The photograph is a close-up of the affected area. Fitzpatrick phototype III: 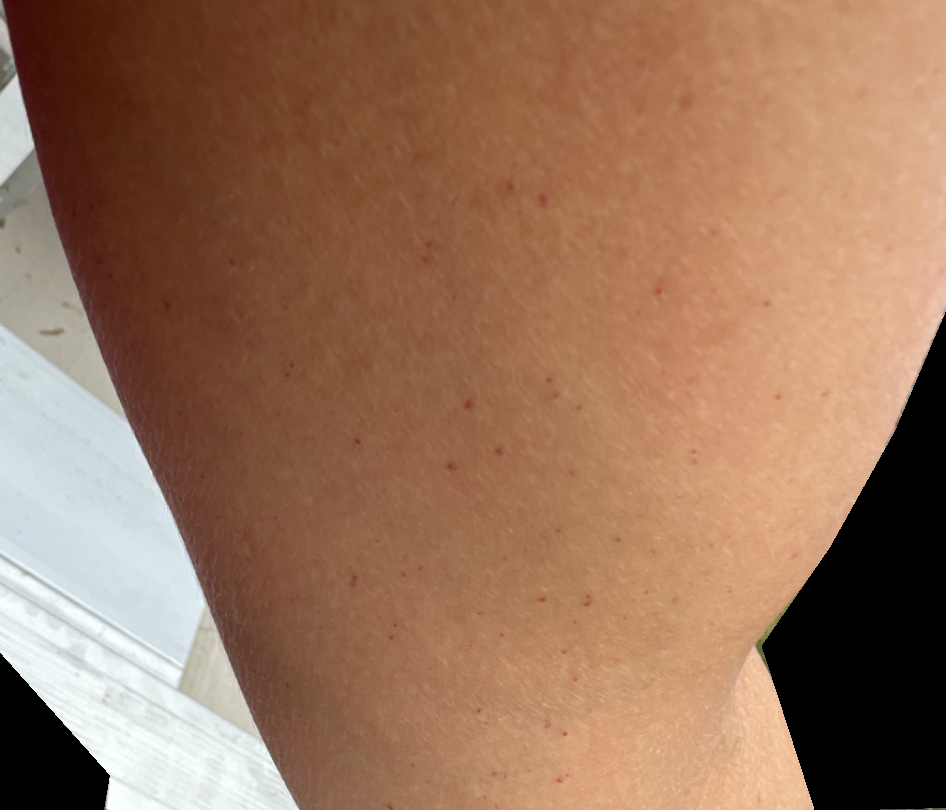The case was difficult to assess from the available photograph.